A female patient aged 59; a clinical photograph showing a skin lesion; the patient says their skin reddens with sun exposure; imaged for a research study, with no referral diagnosis recorded.
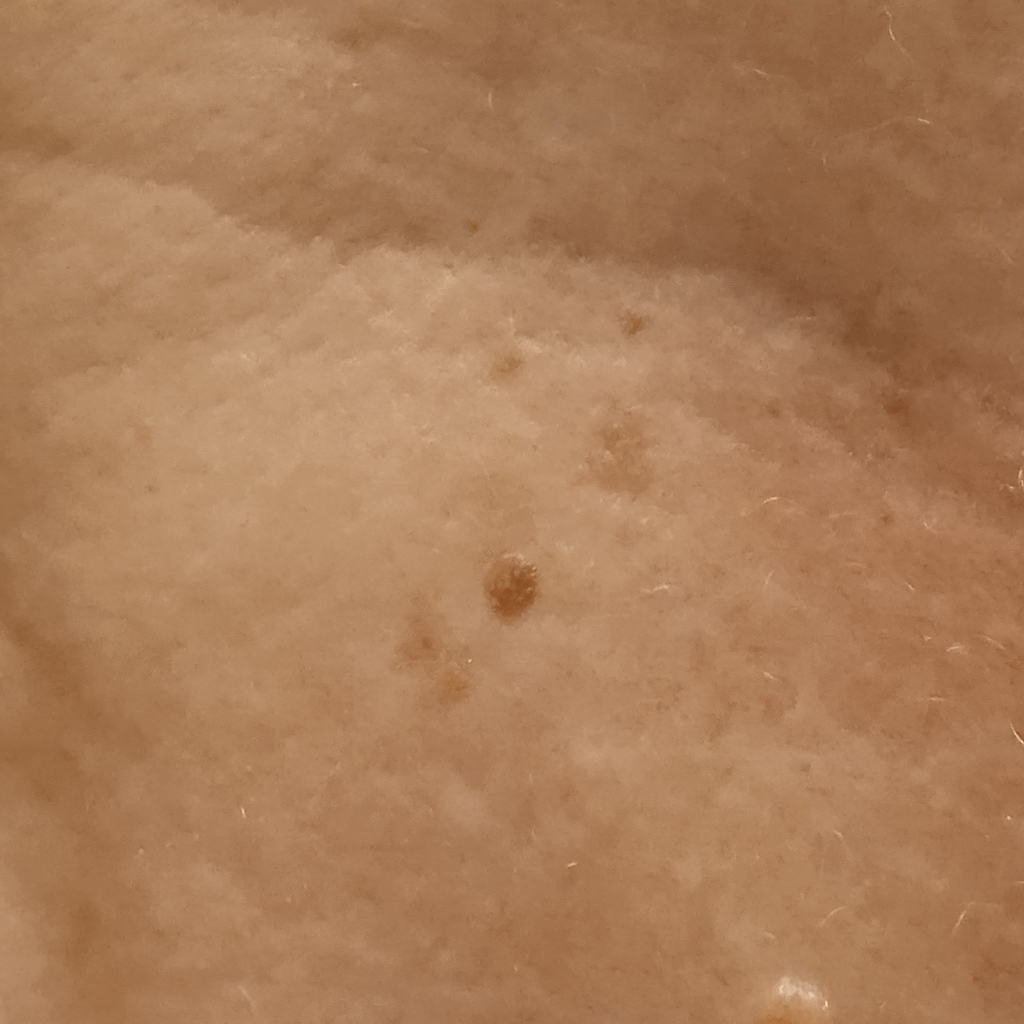Q: What is the anatomic site?
A: the torso
Q: How large is the lesion?
A: 2.2 mm
Q: What was the diagnosis?
A: seborrheic keratosis (dermatologist consensus)